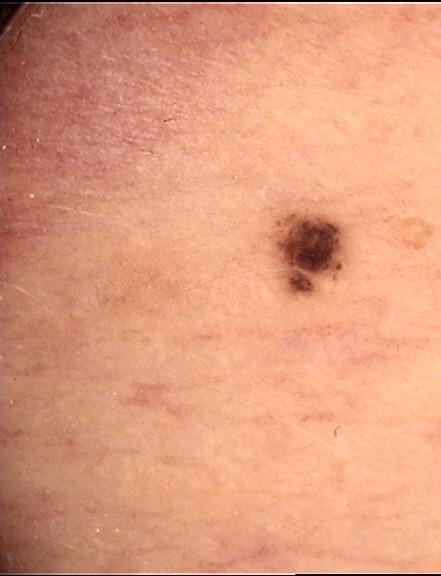diagnostic label=dysplastic junctional nevus (expert consensus).